The photograph is a close-up of the affected area.
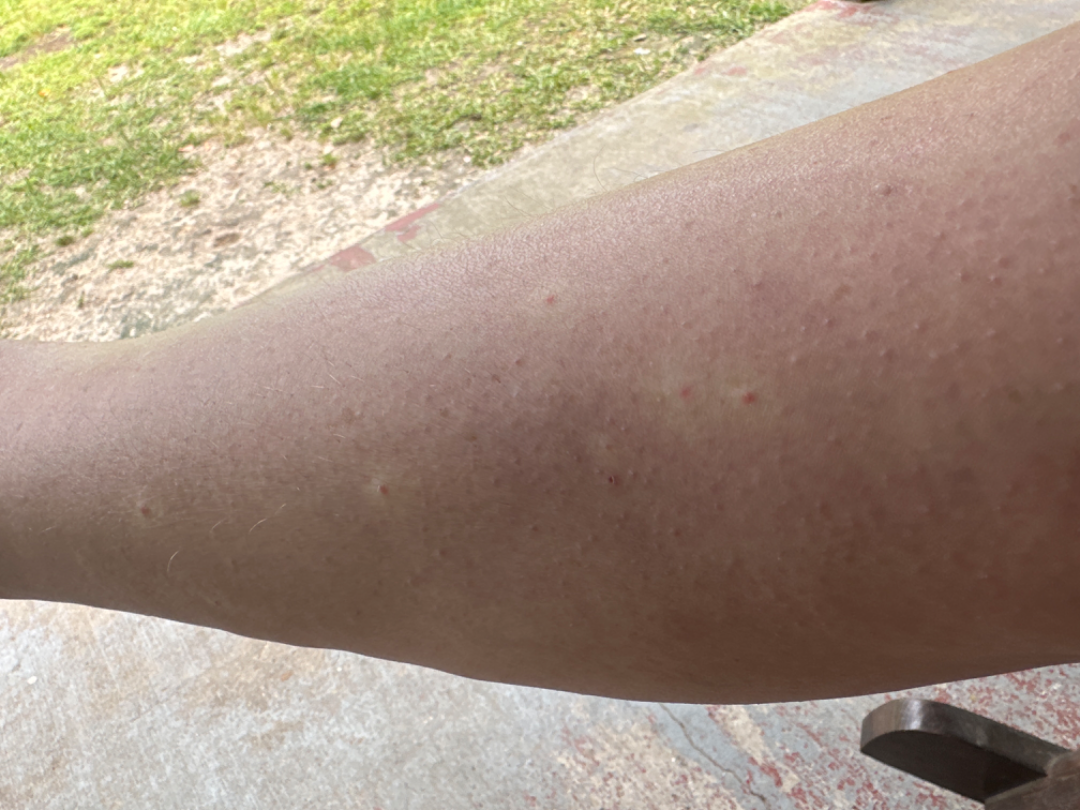Patient information:
Skin tone: Fitzpatrick II; non-clinician graders estimated 2 on the Monk skin tone scale.
Review:
Folliculitis, Insect Bite and Irritant Contact Dermatitis were considered with similar weight.